The photo was captured at an angle:
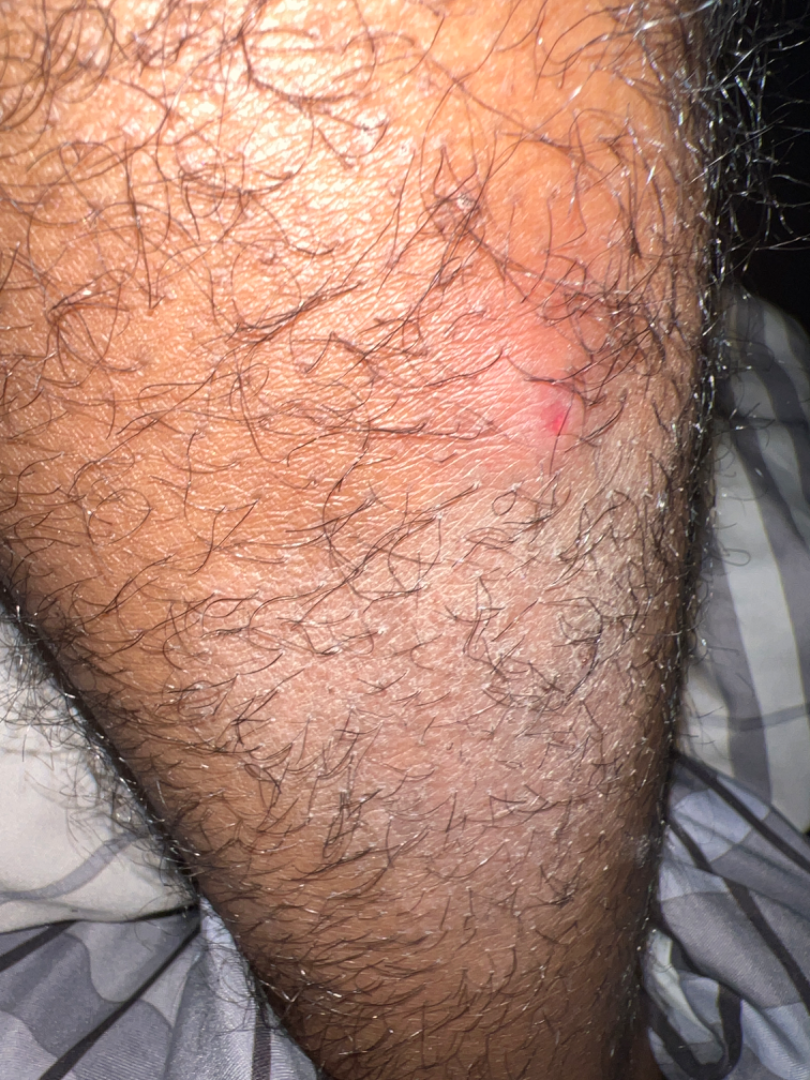Diagnostic features were not clearly distinguishable in this photograph.